Imaged for a research study, with no referral diagnosis recorded. A female patient 54 years of age. Dermoscopy of a skin lesion: 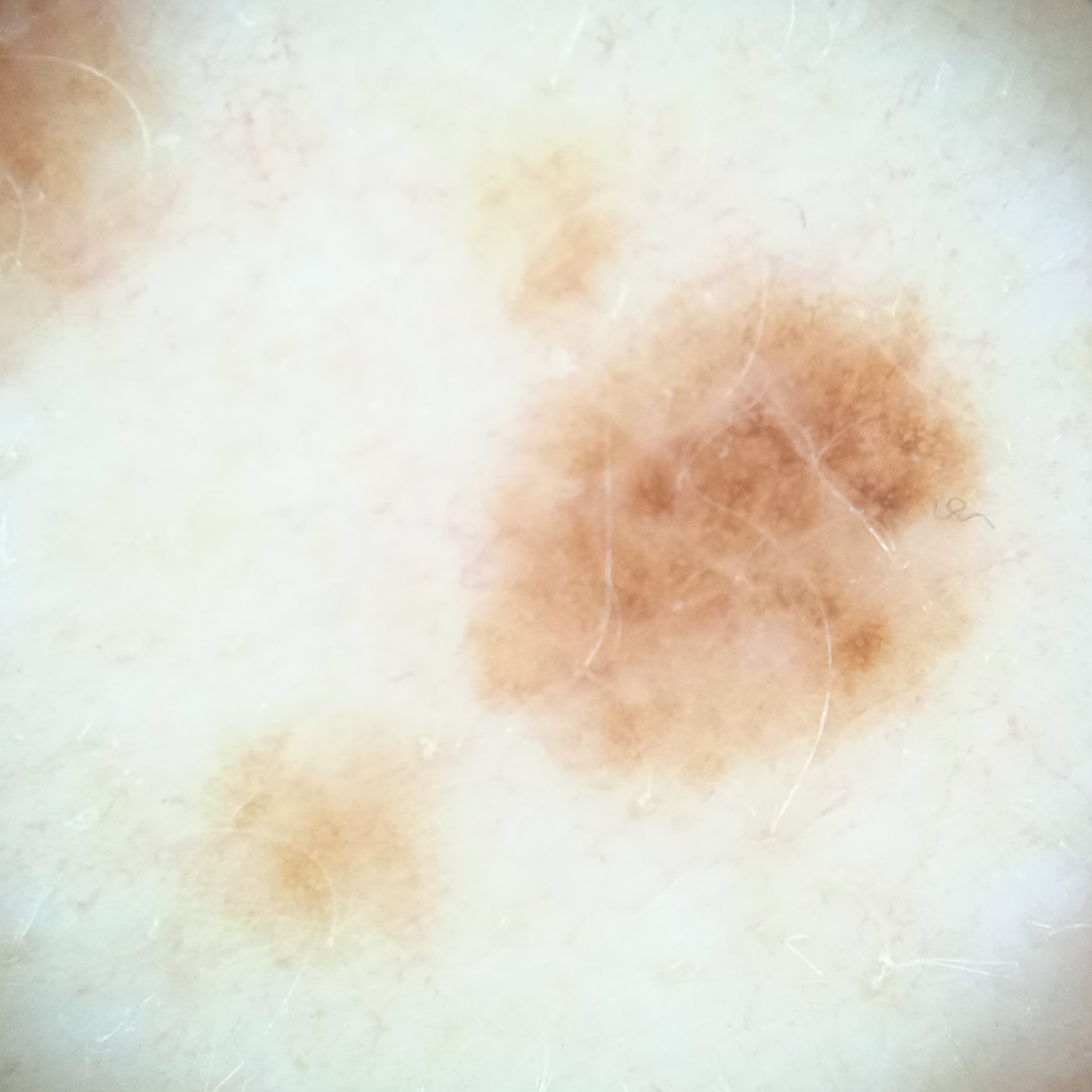Q: Where is the lesion?
A: the back
Q: How large is the lesion?
A: 6.4 mm
Q: What was the diagnosis?
A: atypical (dysplastic) nevus — dermatologist consensus